The patient reports the lesion is raised or bumpy · the subject is 18–29, male · the affected area is the arm · a close-up photograph · skin tone: FST III; non-clinician graders estimated MST 4 (US pool) or 2 (India pool) · self-categorized by the patient as a rash · the lesion is associated with bothersome appearance and itching · present for less than one week: 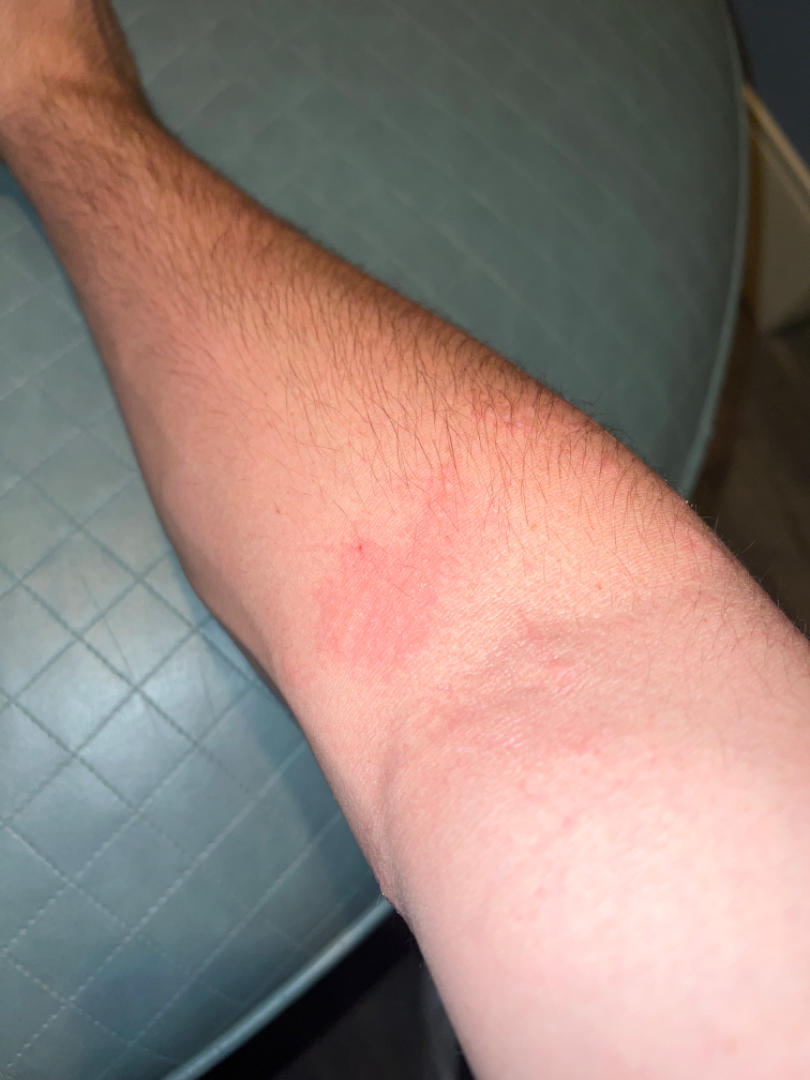- diagnostic considerations · in keeping with Eczema